The lesion involves the head or neck · the patient considered this a rash · present for less than one week · the subject is a female aged 18–29 · the photo was captured at a distance · reported lesion symptoms include itching, enlargement, bothersome appearance and pain · the lesion is described as raised or bumpy: 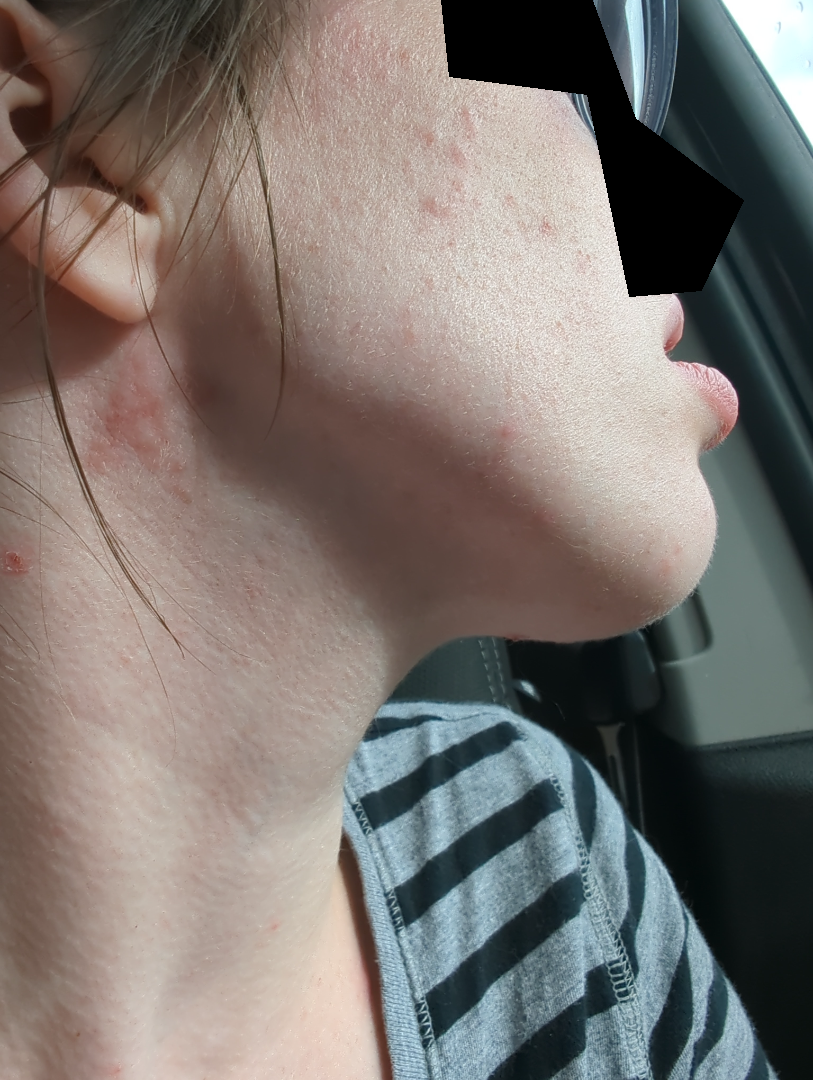Most likely Acne; the differential also includes Seborrheic Dermatitis; possibly Allergic Contact Dermatitis.